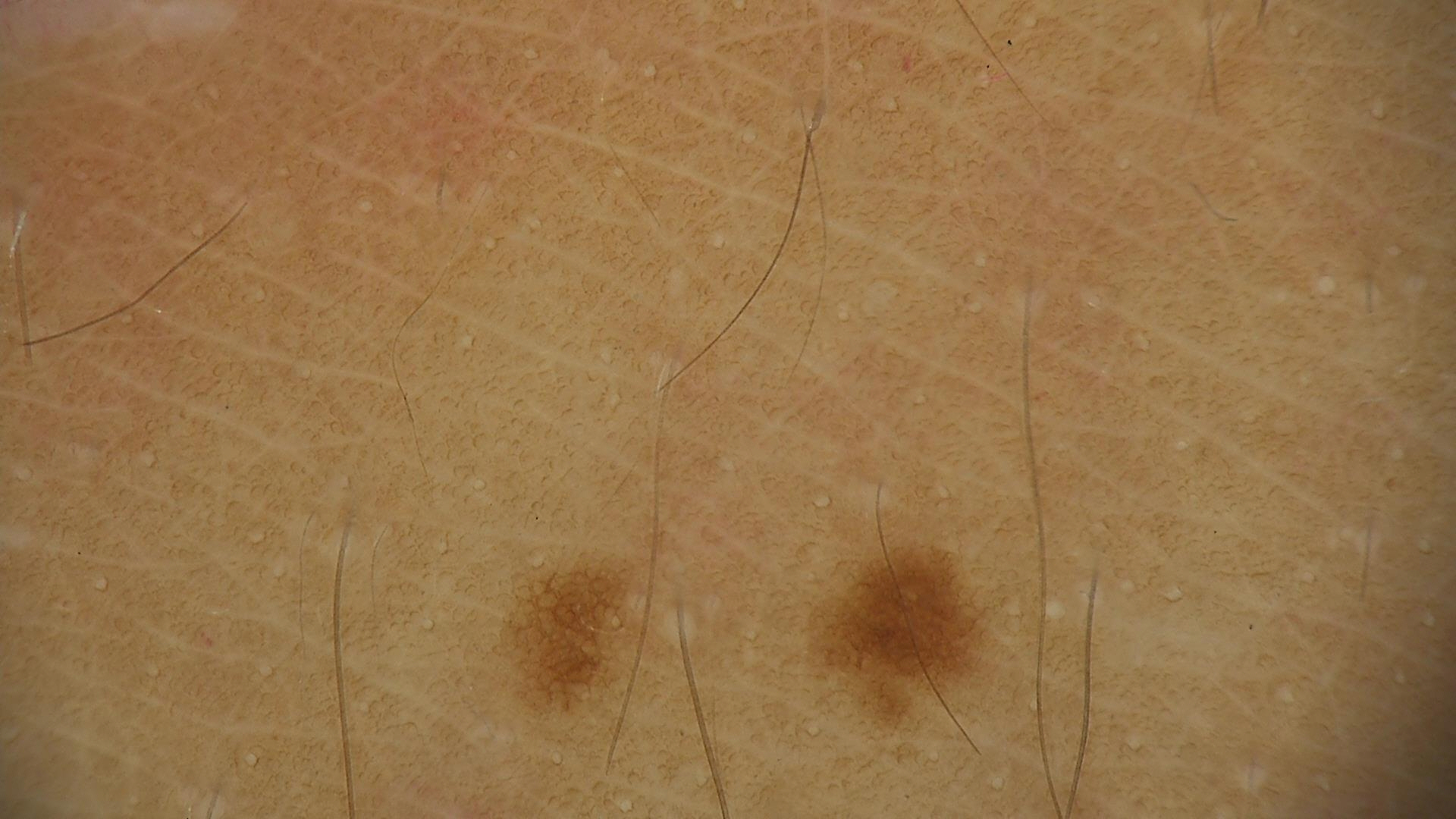image type = dermatoscopy; label = junctional nevus (expert consensus).